Female patient, age 50–59 · the lesion involves the arm, back of the torso, back of the hand and front of the torso · this image was taken at an angle:
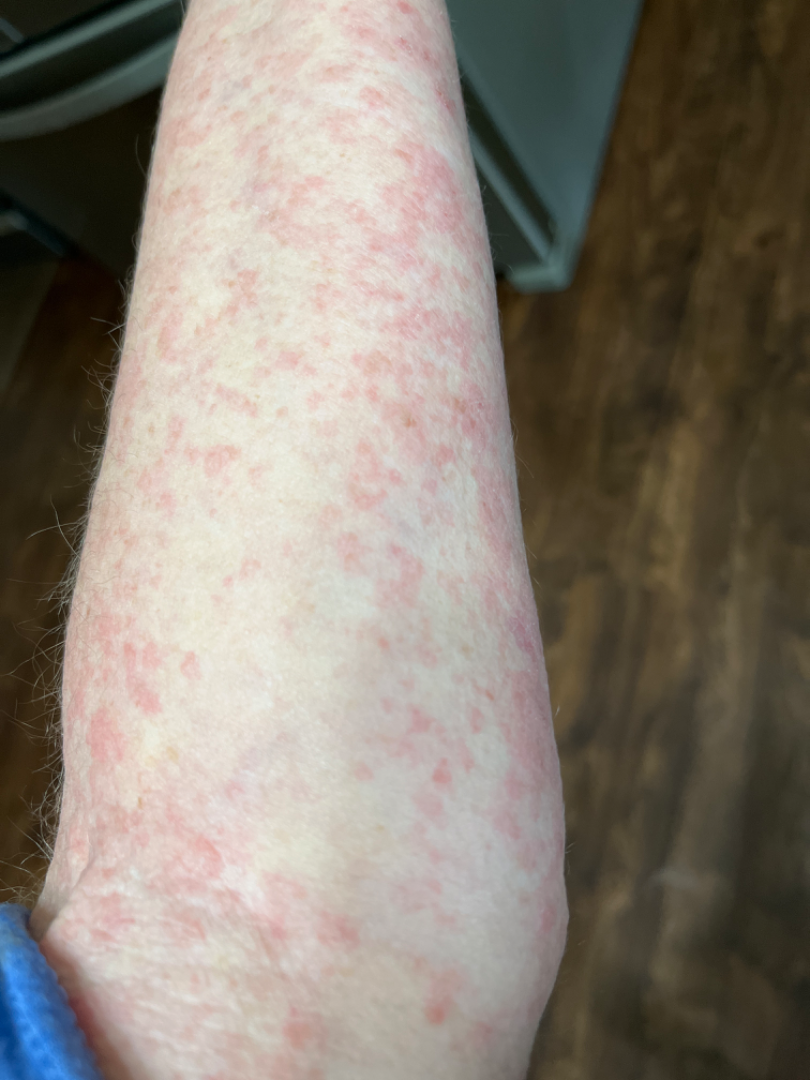On photographic review: the differential includes Drug Rash and Urticaria, with no clear leading consideration.